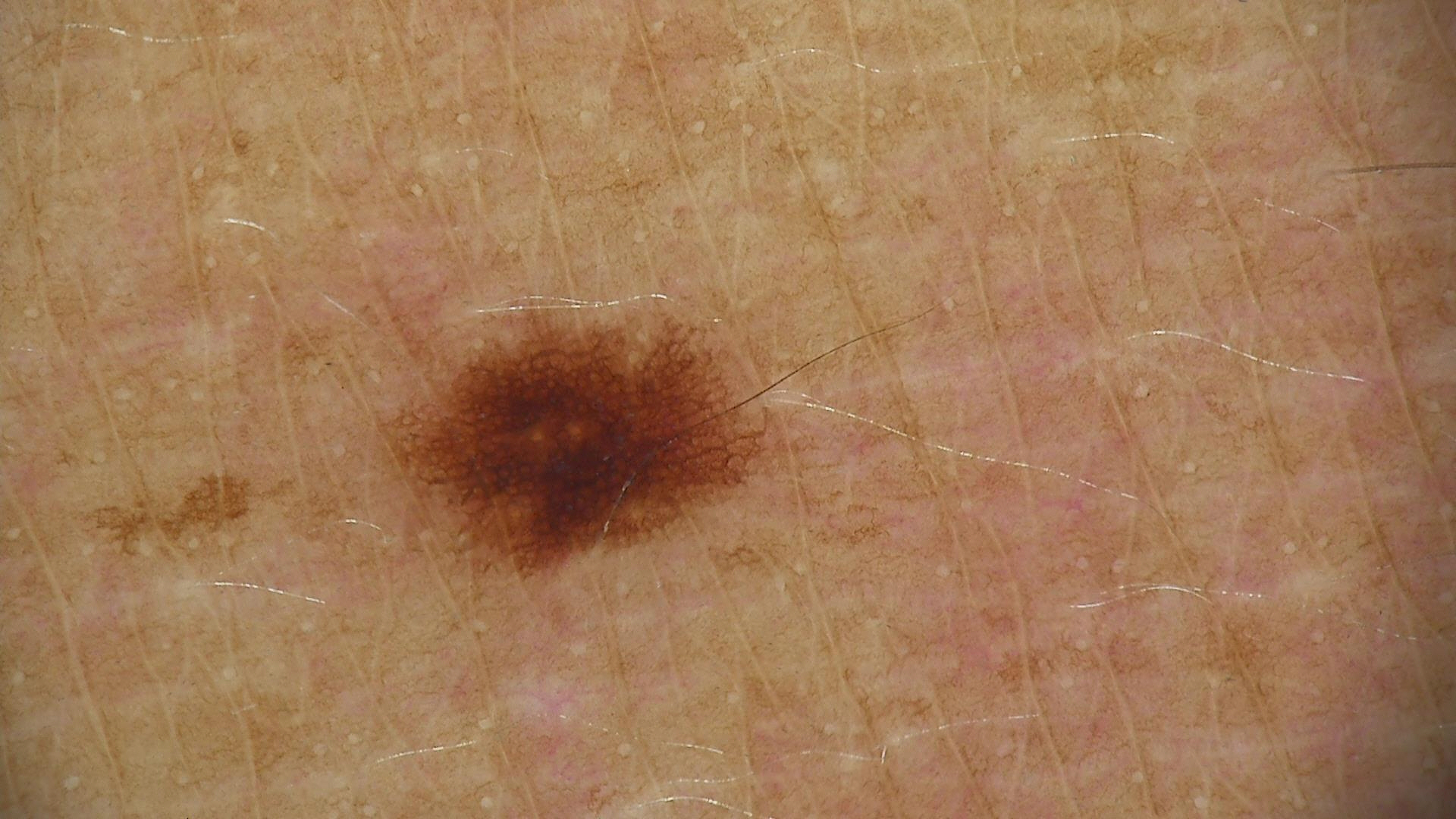A dermoscopic close-up of a skin lesion. The diagnostic label was a benign lesion — a dysplastic junctional nevus.